An image taken at a distance — 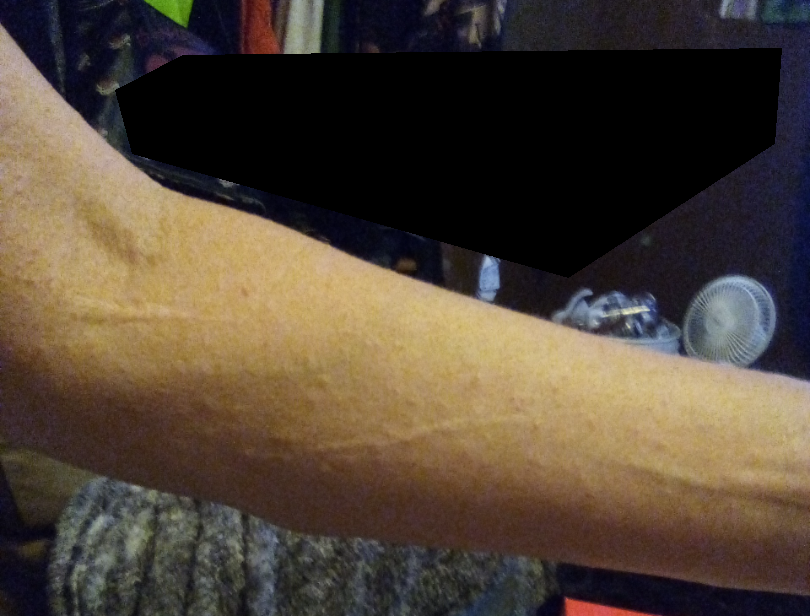Impression:
Urticaria and Allergic Contact Dermatitis were considered with similar weight.